A close-up photograph, the affected area is the leg.
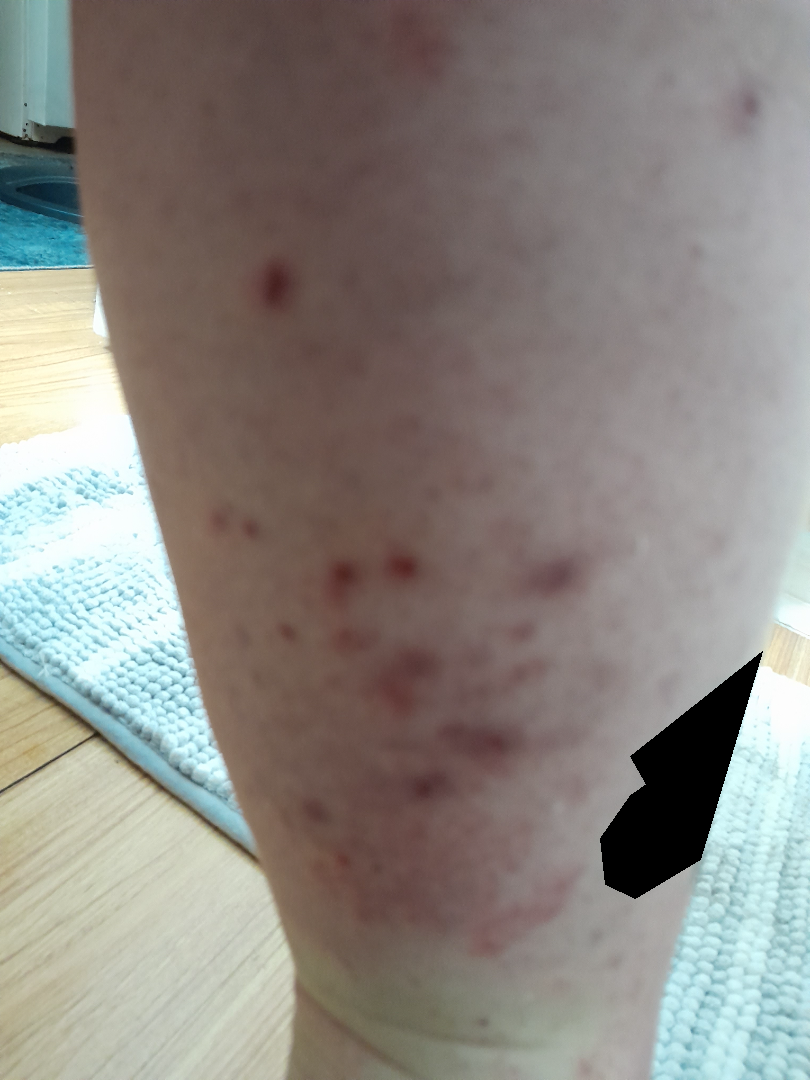The skin findings could not be characterized from the image.